Dermoscopy of a skin lesion.
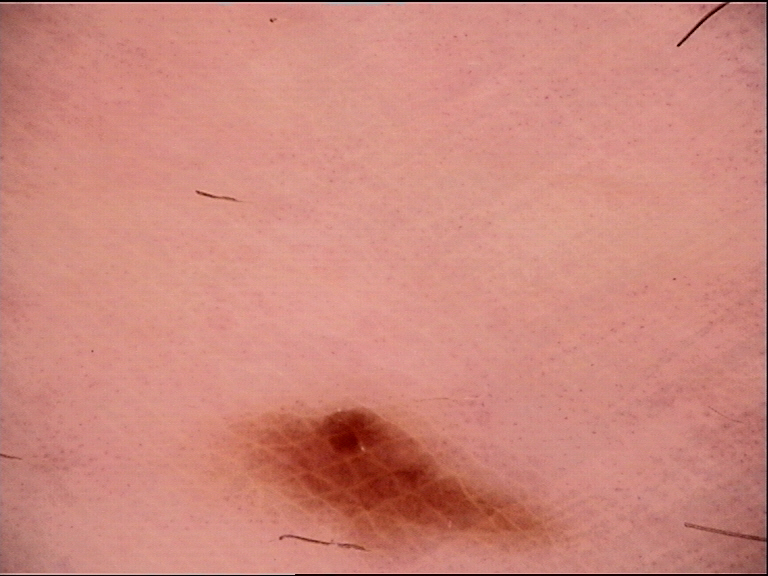subtype=banal; diagnostic label=acral junctional nevus (expert consensus).